A dermoscopy image of a single skin lesion: 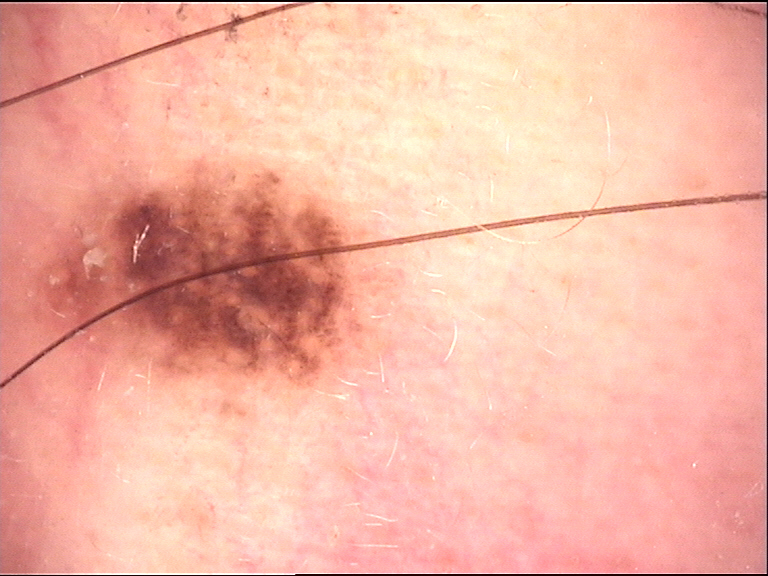The diagnostic label was a dysplastic junctional nevus.